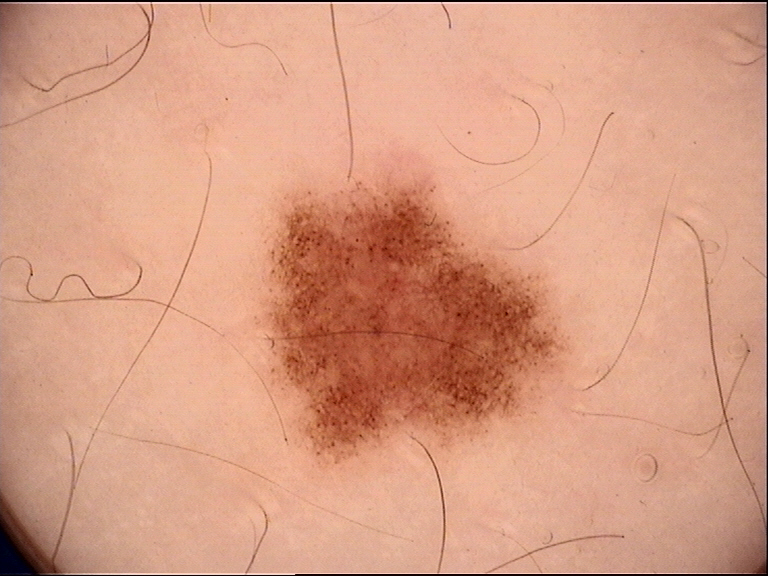Summary:
The morphology is that of a banal lesion.
Conclusion:
The diagnostic label was a junctional nevus.